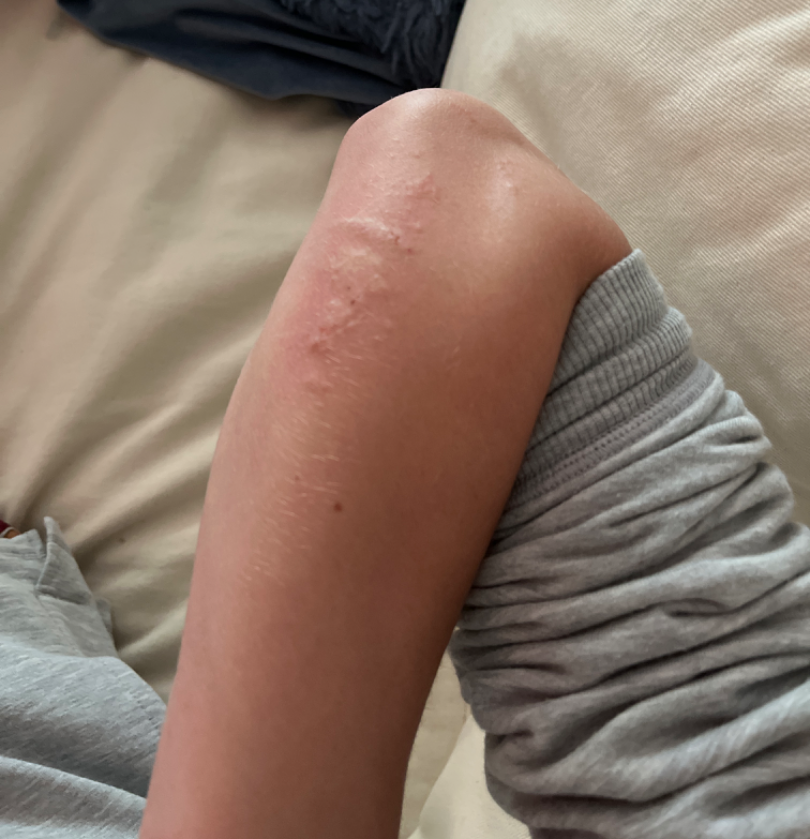  shot_type: at a distance
  body_site: arm
  differential:
    leading:
      - Urticaria